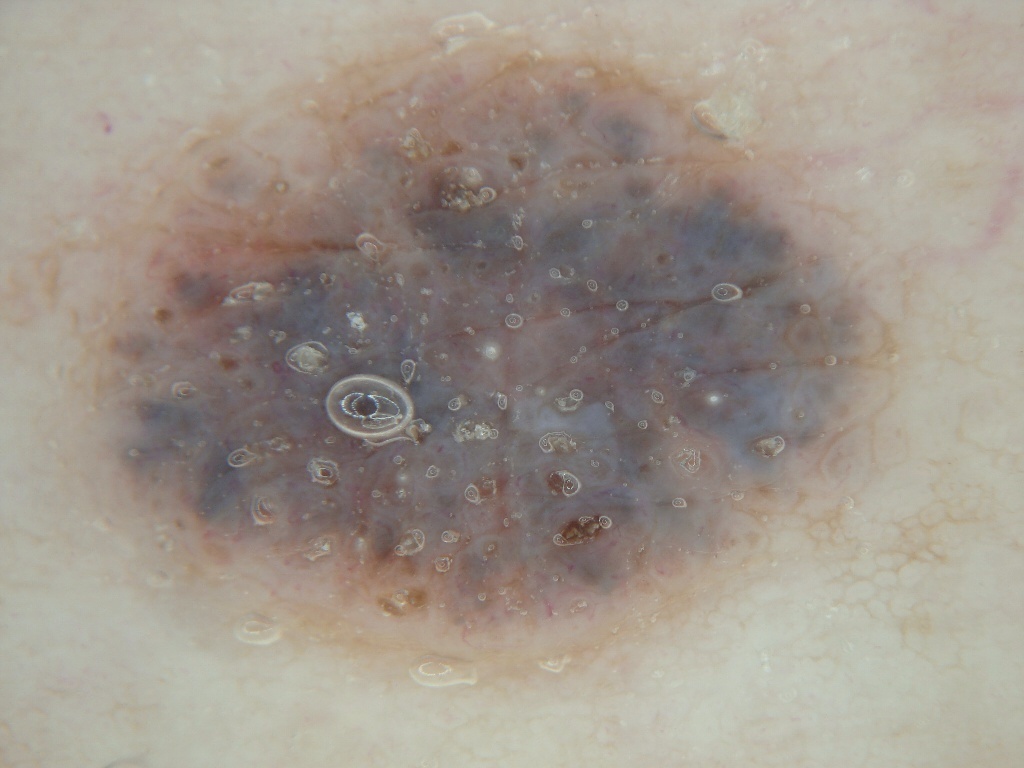Case summary: A skin lesion imaged with a dermatoscope. A female subject, approximately 60 years of age. The dermoscopic pattern shows milia-like cysts. The lesion takes up about 56% of the image. With coordinates (x1, y1, x2, y2), the lesion spans box(2, 36, 926, 663). Impression: Expert review diagnosed this as a melanocytic nevus, a benign lesion.